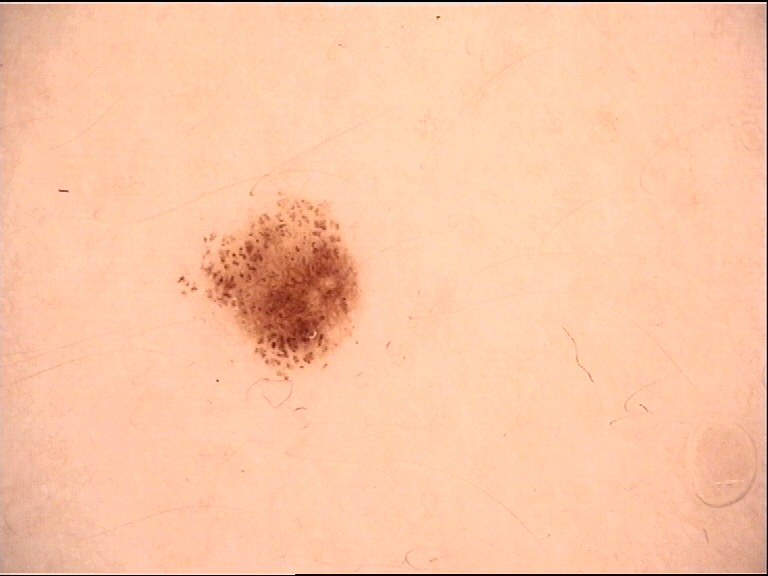label: dysplastic junctional nevus (expert consensus).